By history, tobacco use, prior malignancy (patient or family), prior skin cancer (patient or family), and alcohol use · a smartphone photograph of a skin lesion — 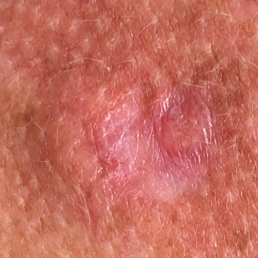Clinical context:
The lesion was found on the chest. Measuring about 12 × 12 mm. By the patient's account, the lesion itches, has grown, and is elevated, but has not changed and does not hurt.
Conclusion:
Histopathological examination showed a basal cell carcinoma.